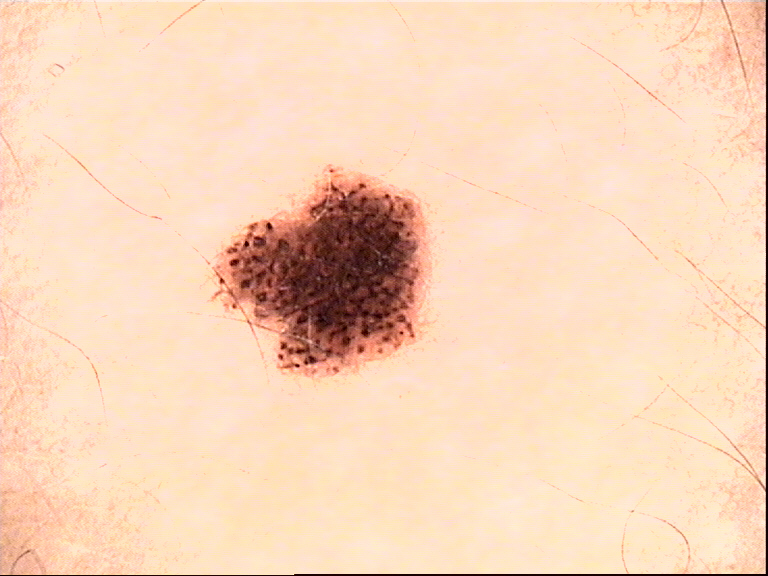image type=dermatoscopy
subtype=banal
diagnostic label=compound nevus (expert consensus)